The subject is 30–39, female; close-up view: 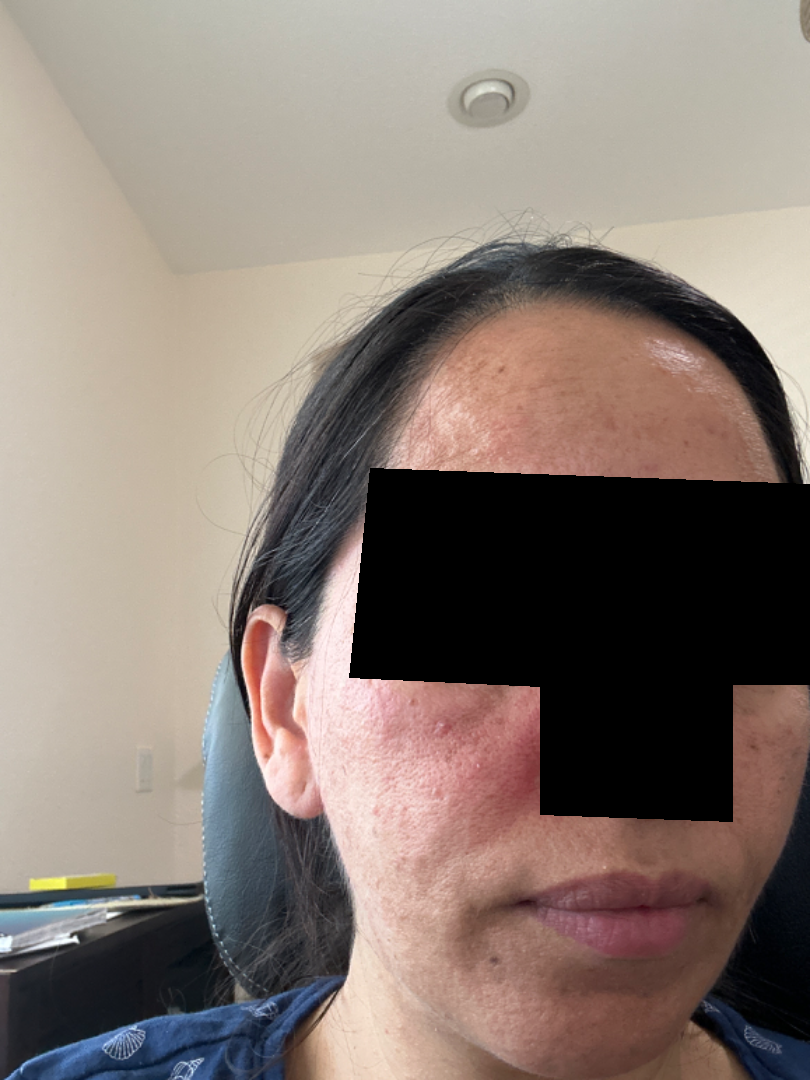Q: Any systemic symptoms?
A: none reported
Q: What symptoms does the patient report?
A: burning, pain, itching and bothersome appearance
Q: Patient's own categorization?
A: a rash
Q: What conditions are considered?
A: a single dermatologist reviewed the case: favoring Rosacea; with consideration of Allergic Contact Dermatitis; also consider Systemic lupus erythematosus-related syndrome